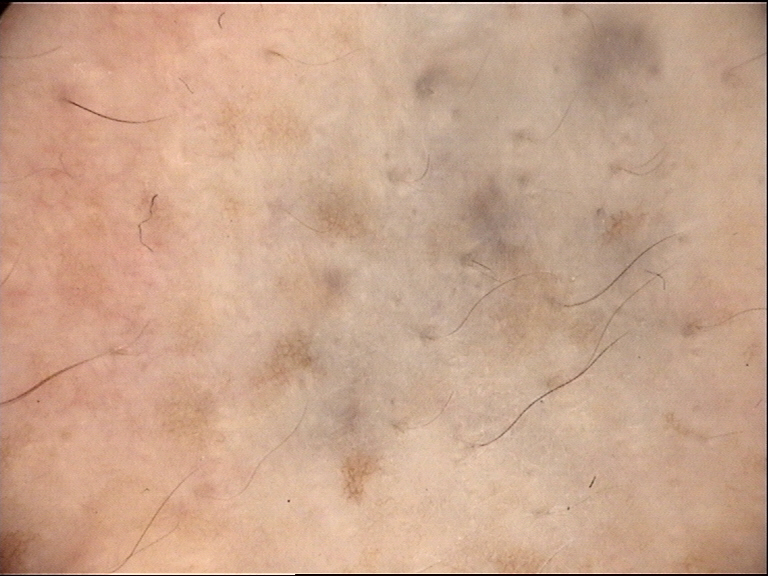class = blue nevus (expert consensus)